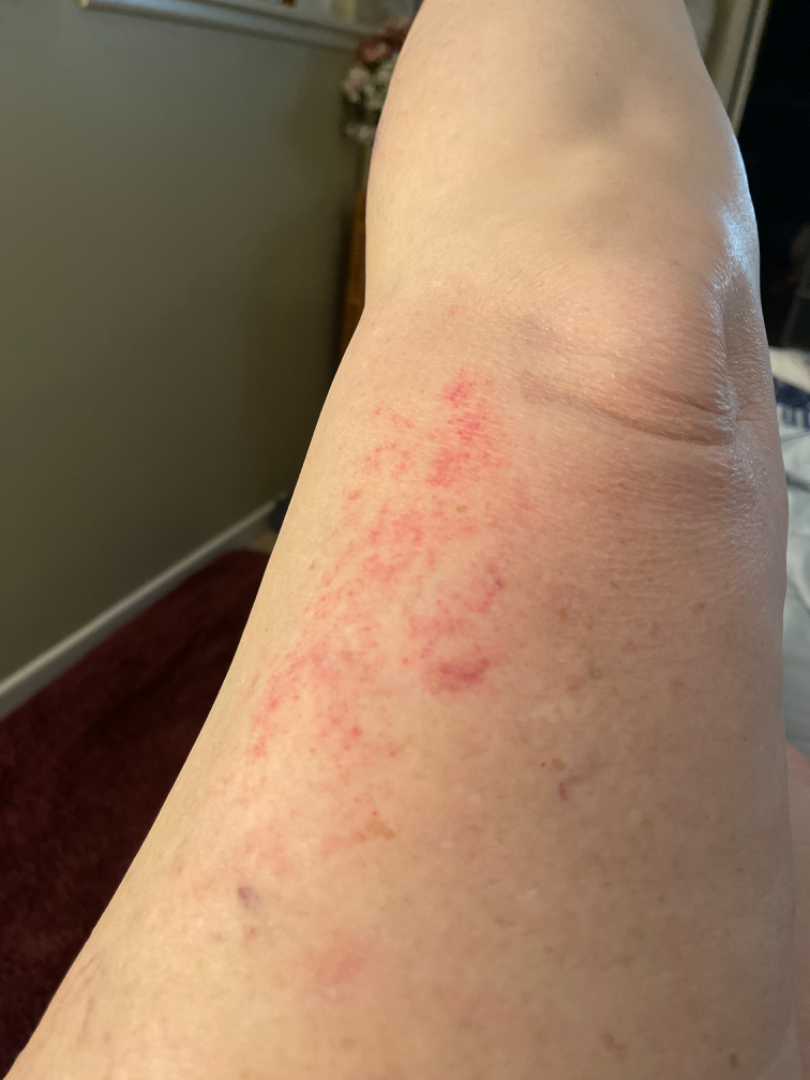assessment: could not be assessed
texture: flat
body_site: leg
shot_type: at a distance
duration: about one day
patient_category: a rash